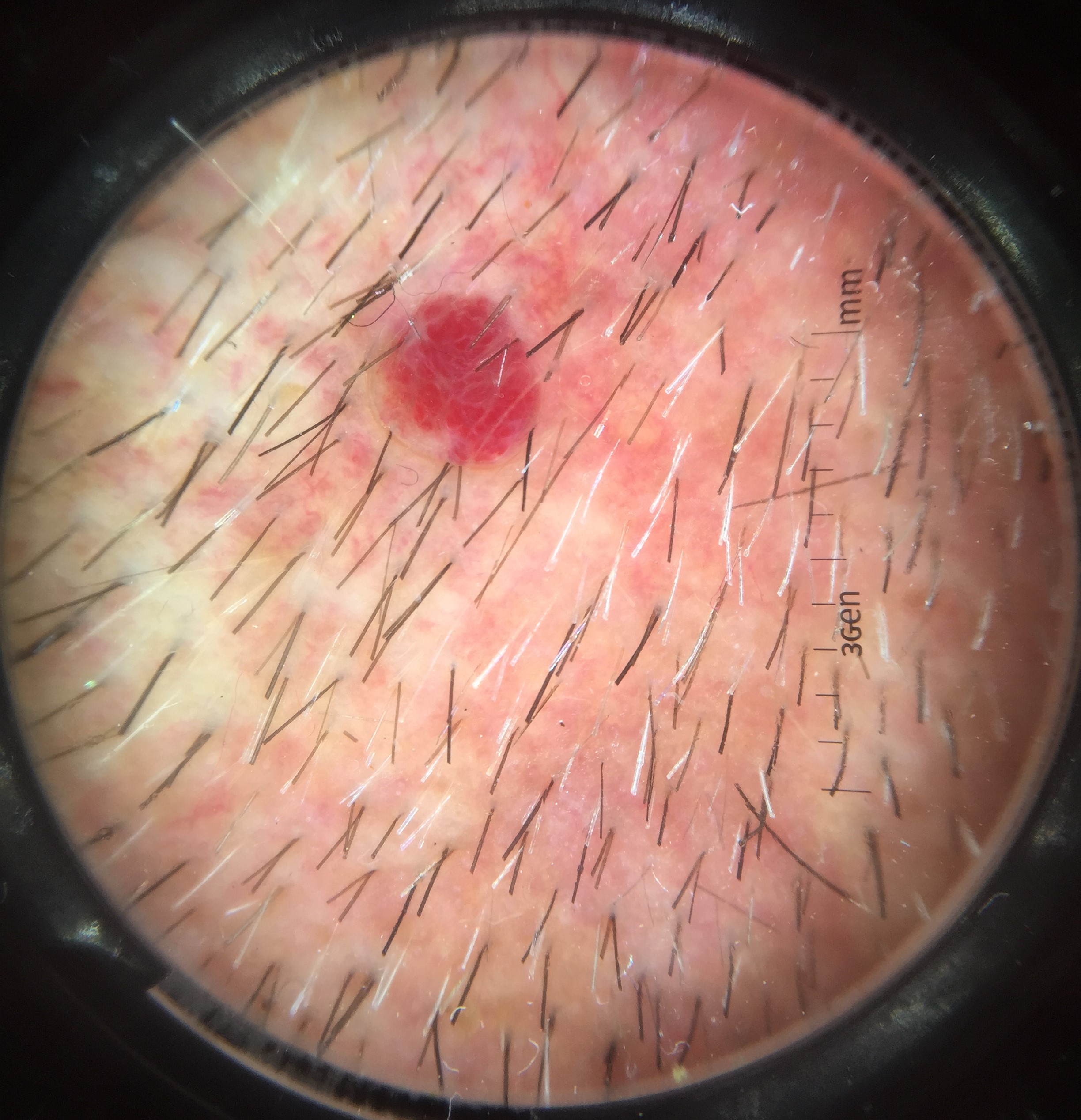A dermoscopic close-up of a skin lesion.
Classified as a vascular lesion — a hemangioma.